Female patient, age 30–39 · the lesion involves the leg and arm · the photograph was taken at an angle:
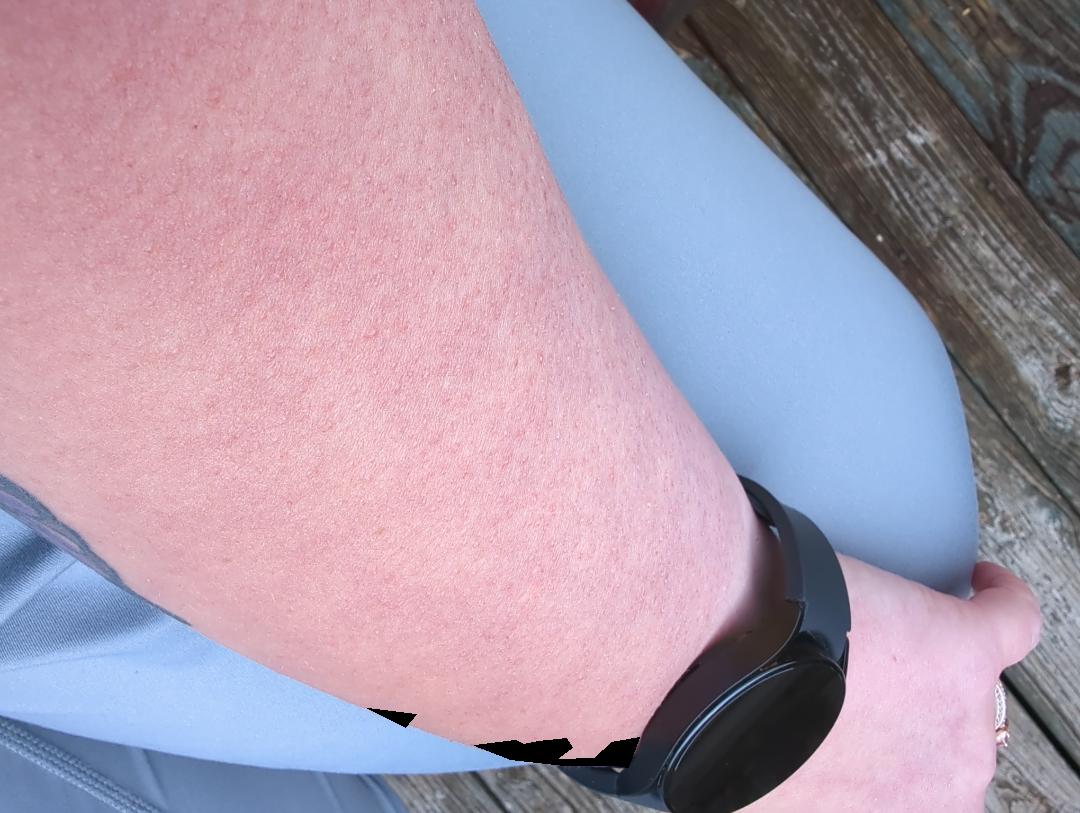The case was difficult to assess from the available photograph.